The photograph is a close-up of the affected area. The lesion involves the back of the hand. The contributor is 18–29, female:
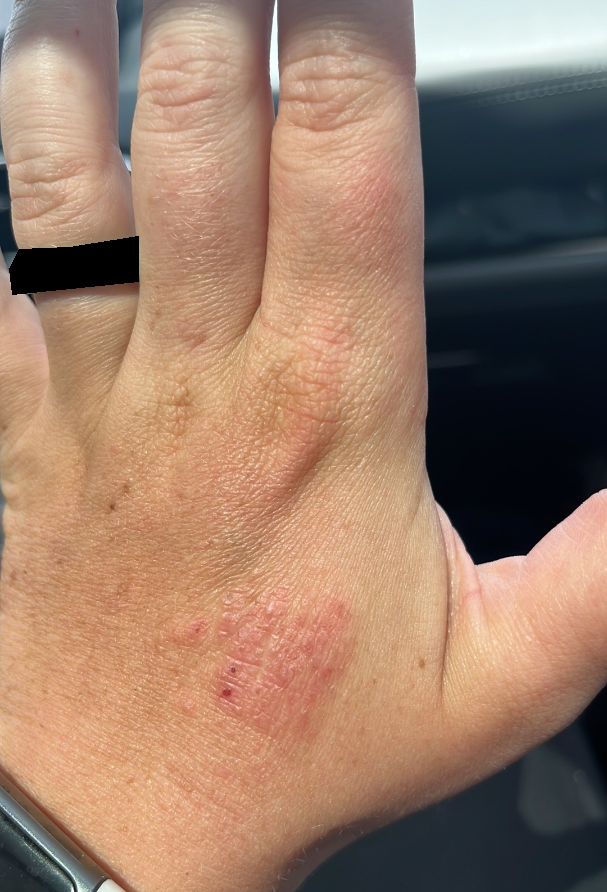Clinical context: The condition has been present for one to four weeks. The patient indicates the lesion is rough or flaky. The patient described the issue as a rash. Assessment: The impression was split between Lichen Simplex Chronicus and Allergic Contact Dermatitis.